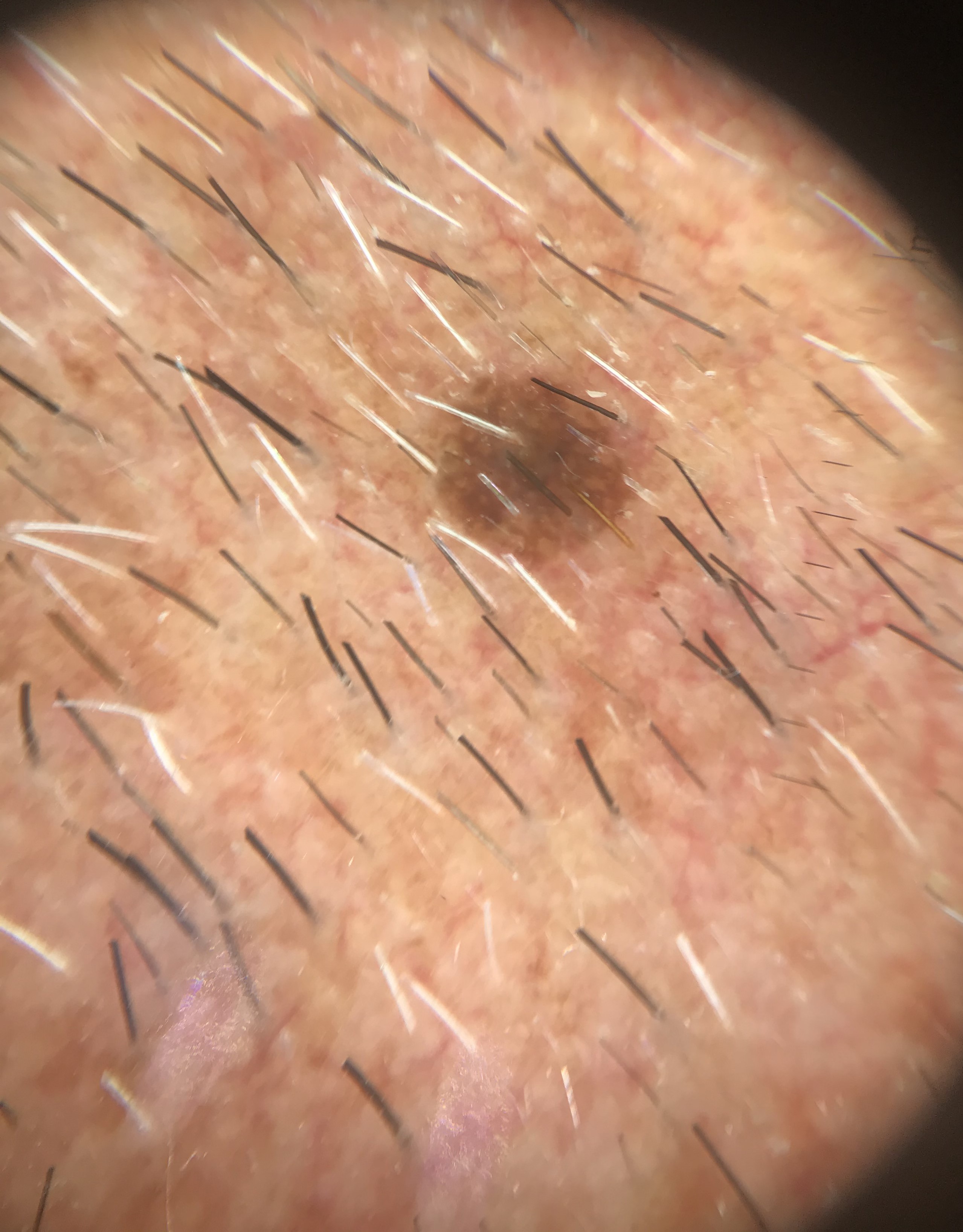assessment: seborrheic keratosis (expert consensus).